A dermoscopy image of a single skin lesion:
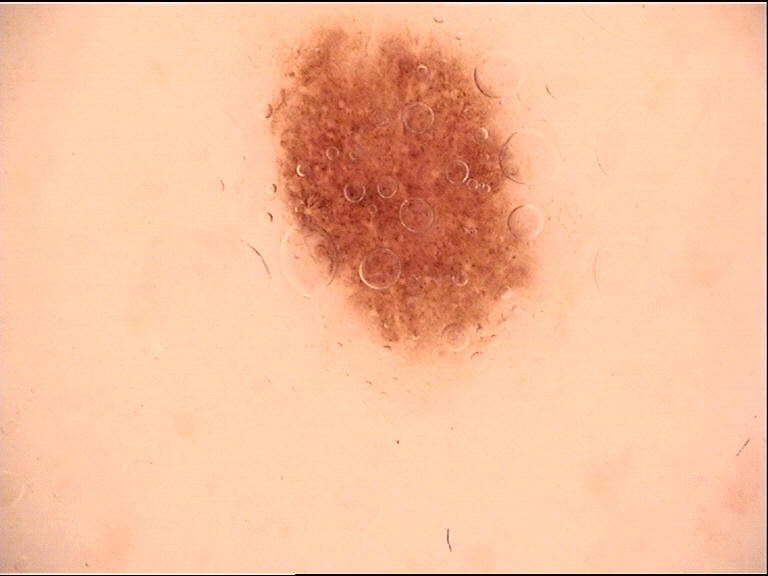| feature | finding |
|---|---|
| assessment | dysplastic junctional nevus (expert consensus) |